A female patient 66 years old · a clinical photo of a skin lesion taken with a smartphone:
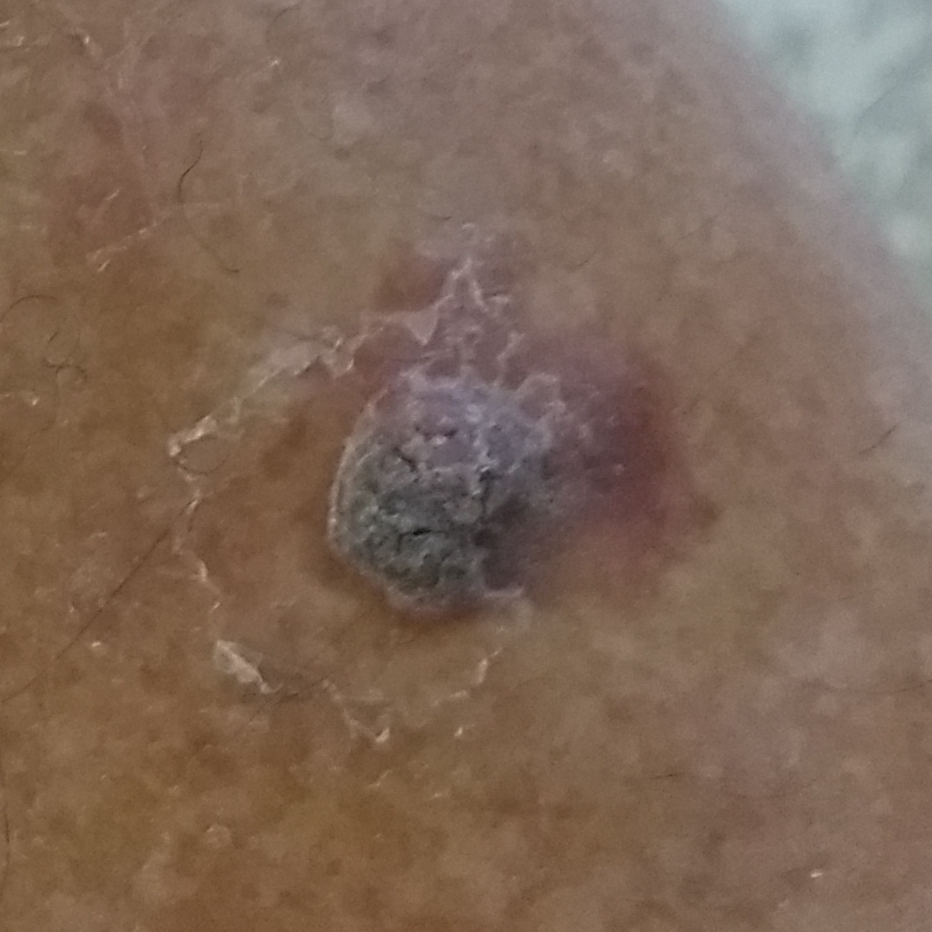The lesion is located on a thigh. Per patient report, the lesion is elevated. Histopathologically confirmed as an actinic keratosis.